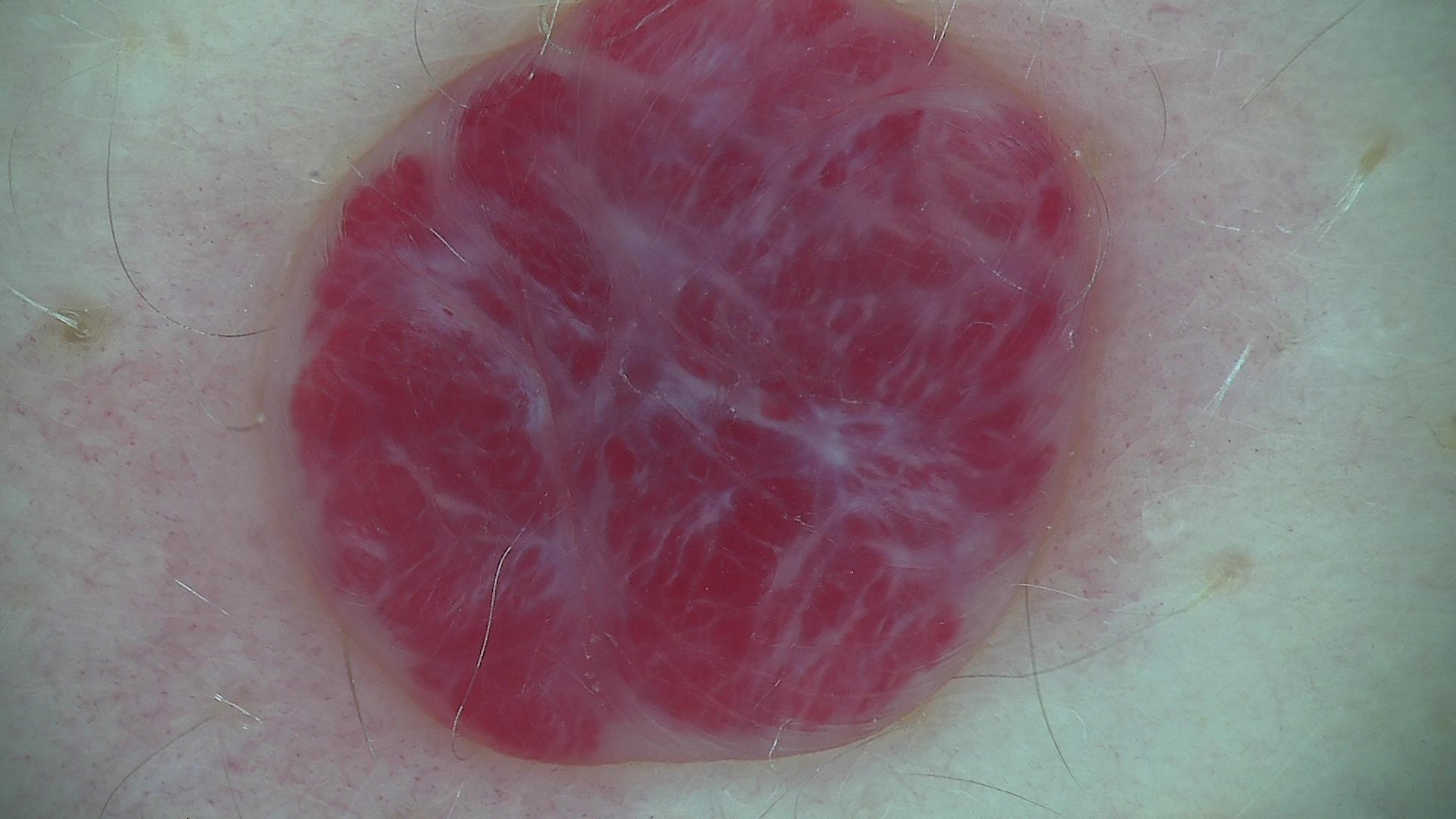image = dermoscopy, assessment = hemangioma (expert consensus).